A clinical photo of a skin lesion taken with a smartphone · recorded as Fitzpatrick II: 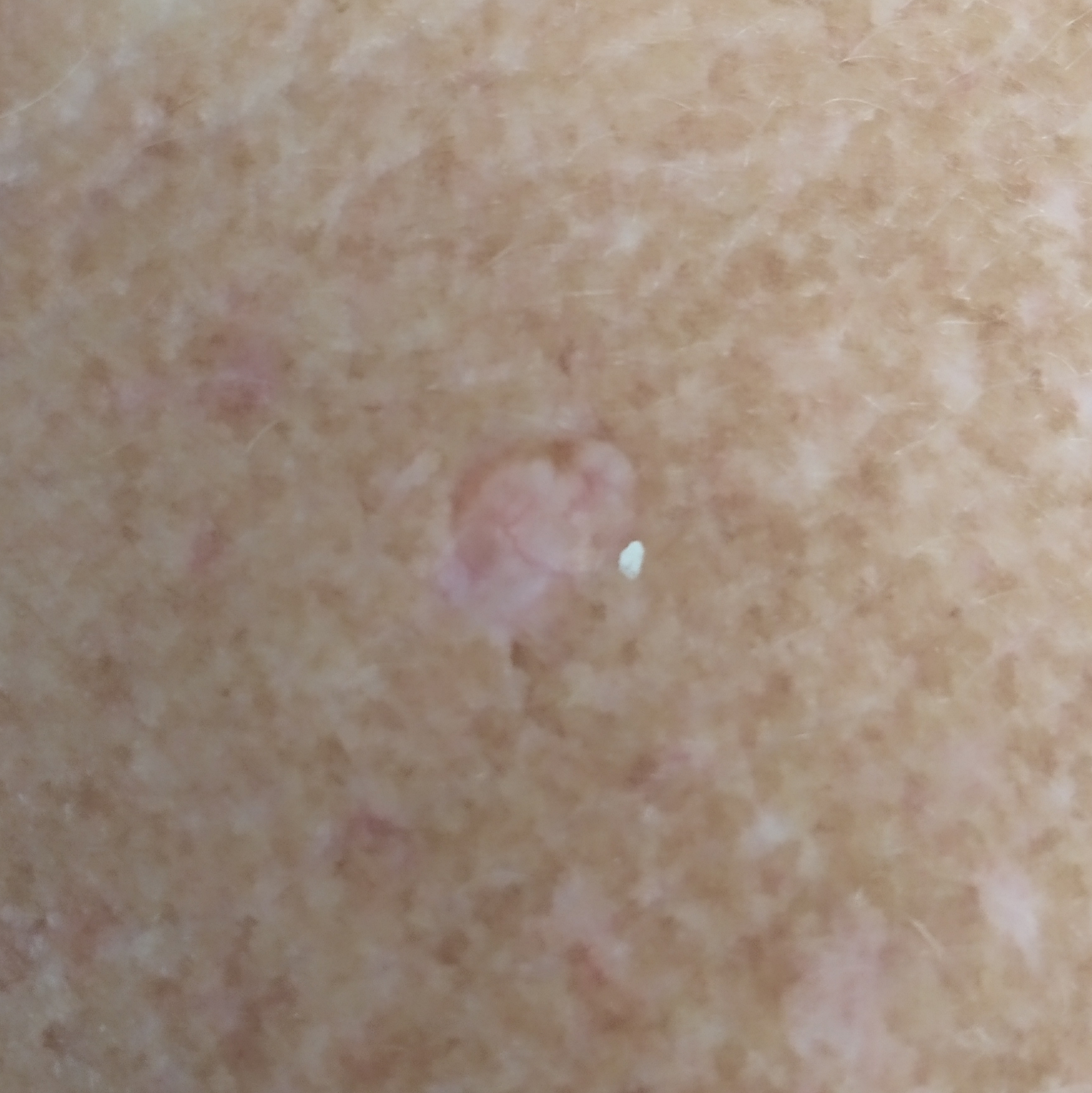Case summary:
The lesion is on the neck. Measuring about 9 × 8 mm. The patient describes that the lesion is elevated.
Conclusion:
Histopathology confirmed a basal cell carcinoma.